A smartphone photograph of a skin lesion — 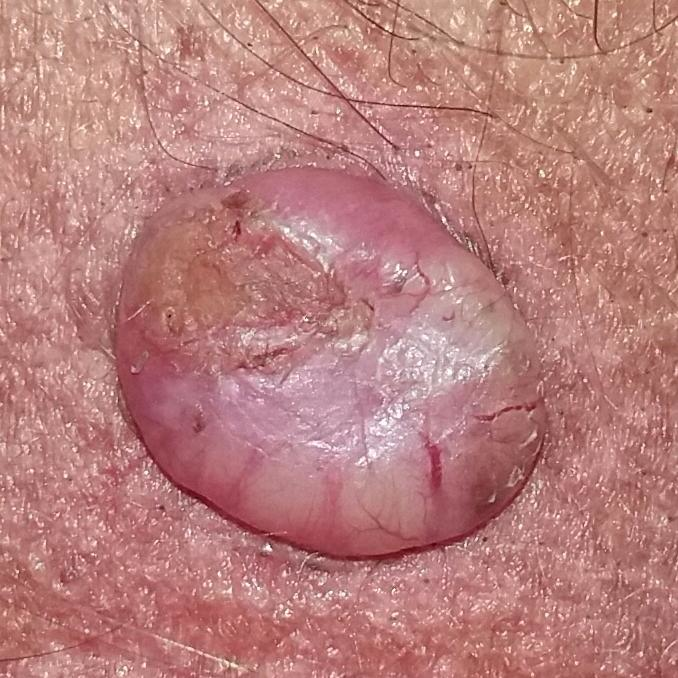Q: Where on the body is the lesion?
A: the neck
Q: How large is the lesion?
A: 10x8 mm
Q: What does the patient describe?
A: elevation, pain, itching, growth, bleeding
Q: What is the diagnosis?
A: basal cell carcinoma (biopsy-proven)